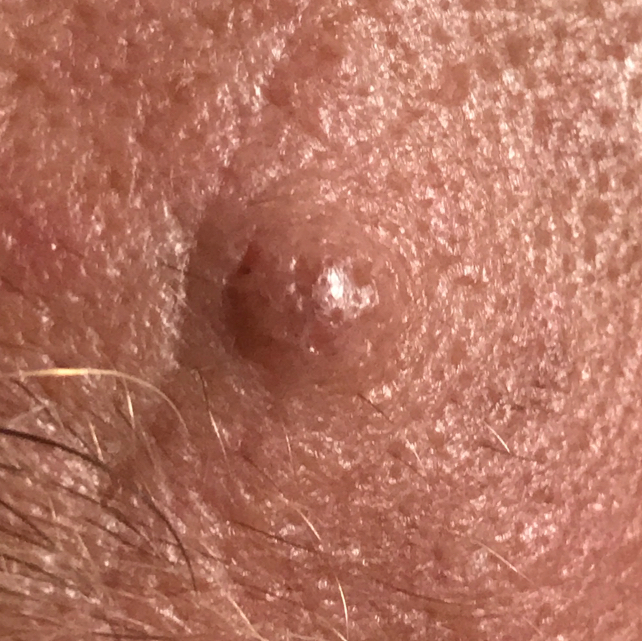A subject in their early 50s.
A clinical close-up photograph of a skin lesion.
The lesion is on the face.
The patient reports that the lesion is elevated.
Consistent with a nevus.